Self-categorized by the patient as a hair problem; the lesion involves the arm; the lesion is described as raised or bumpy; this image was taken at an angle; present for less than one week; reported lesion symptoms include burning; no relevant systemic symptoms — 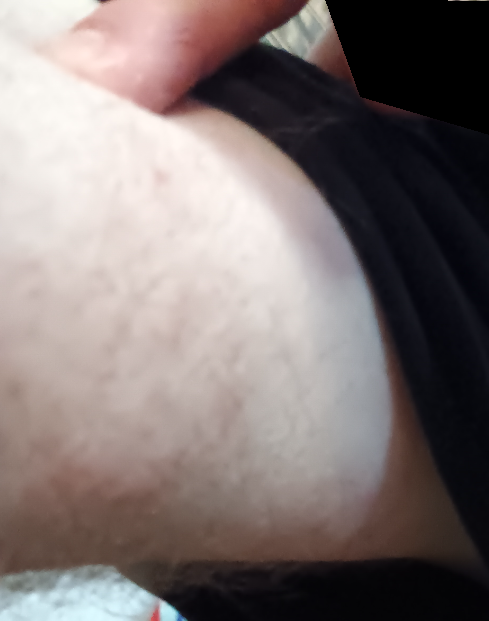The condition could not be reliably identified from the image.